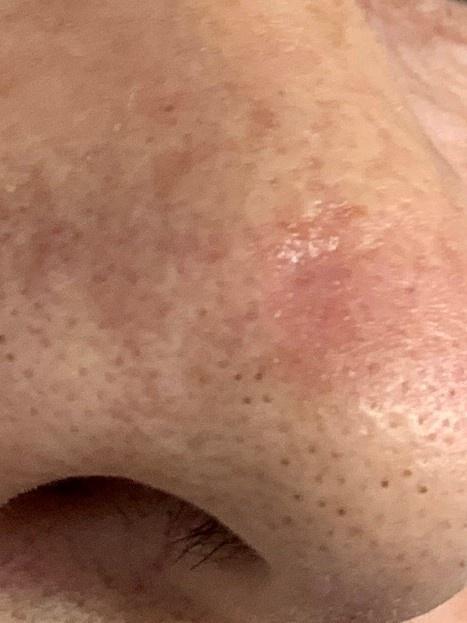A female subject aged 78-82.
A clinical overview photograph of a skin lesion.
The lesion is located on the head or neck.
Histopathological examination showed a lesion of adnexal (follicular) origin — a basal cell carcinoma.